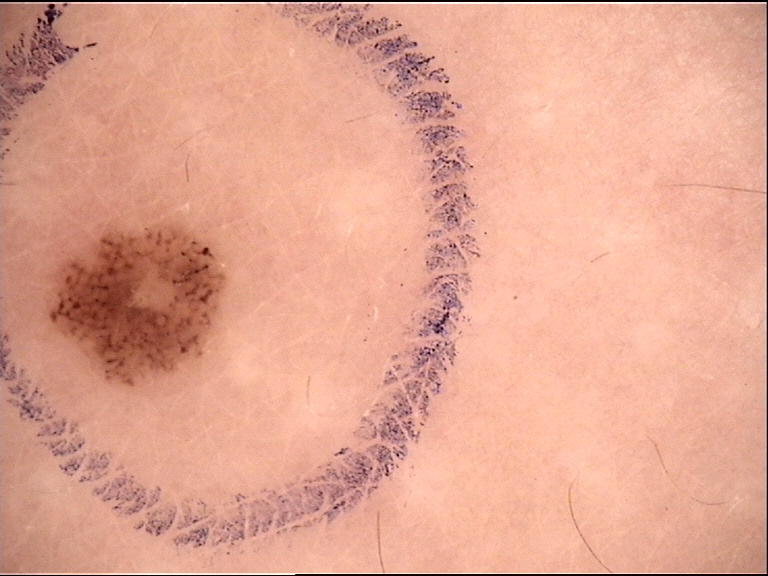Findings: Dermoscopy of a skin lesion. Impression: Labeled as a dysplastic junctional nevus.